A female patient aged 73 to 77, this is a dermoscopic photograph of a skin lesion.
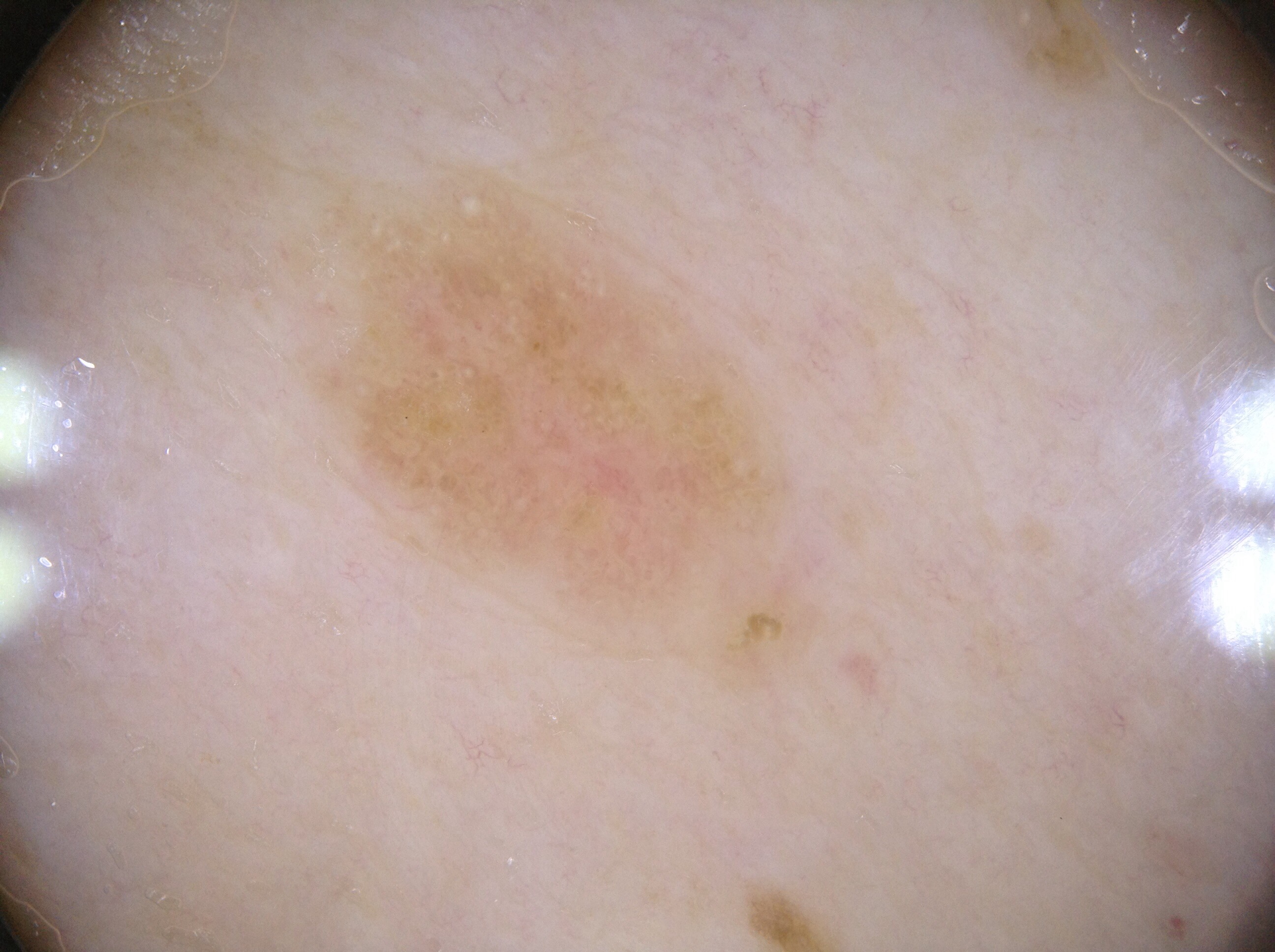{
  "dermoscopic_features": {
    "present": [
      "milia-like cysts"
    ],
    "absent": [
      "negative network",
      "streaks",
      "pigment network"
    ]
  },
  "lesion_extent": "moderate",
  "lesion_location": {
    "bbox_xyxy": [
      339,
      201,
      767,
      595
    ]
  },
  "diagnosis": {
    "name": "seborrheic keratosis",
    "malignancy": "benign",
    "lineage": "keratinocytic",
    "provenance": "clinical"
  }
}